A dermoscopy image of a single skin lesion:
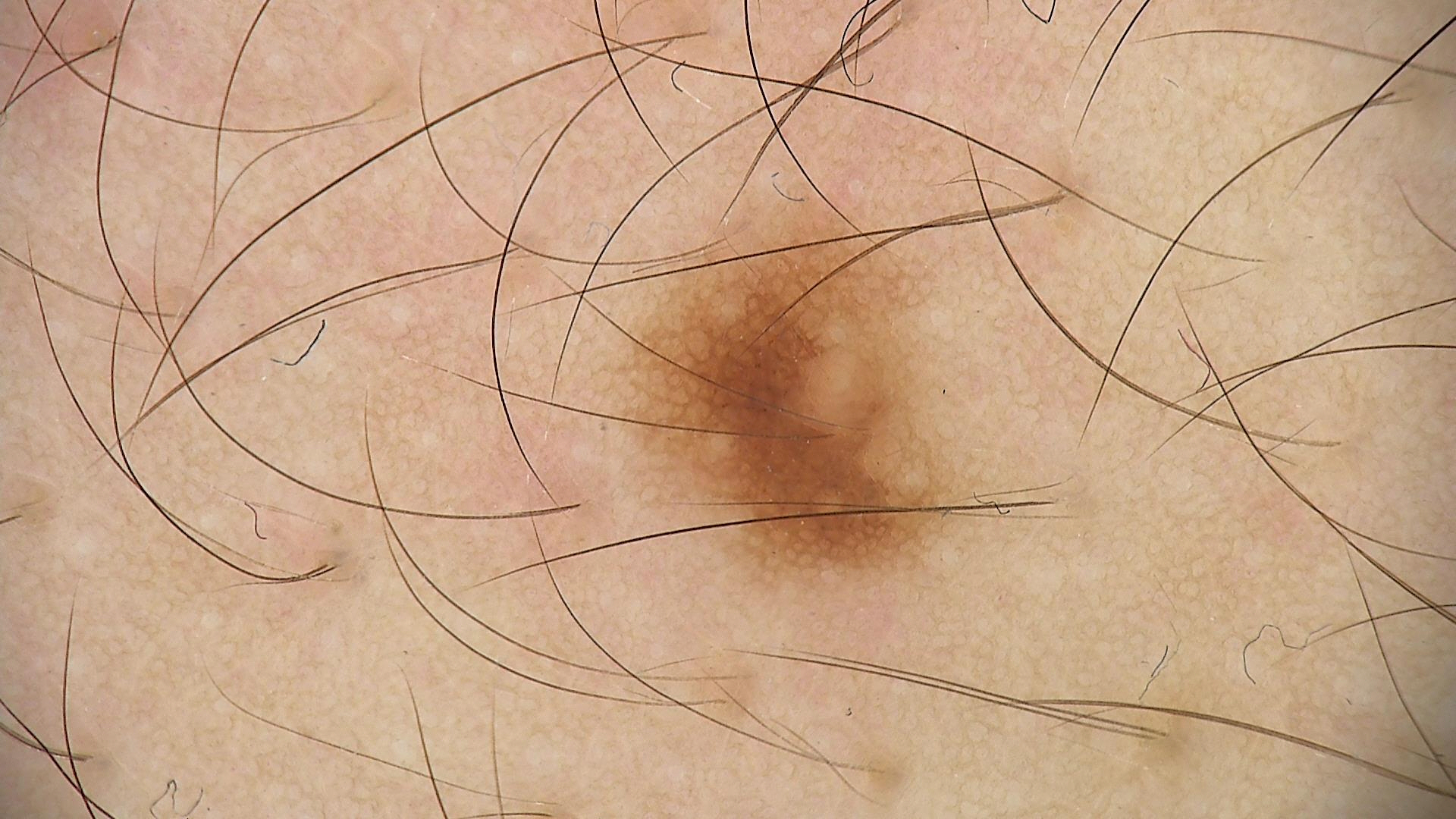class = dysplastic junctional nevus (expert consensus).